A skin lesion imaged with a dermatoscope.
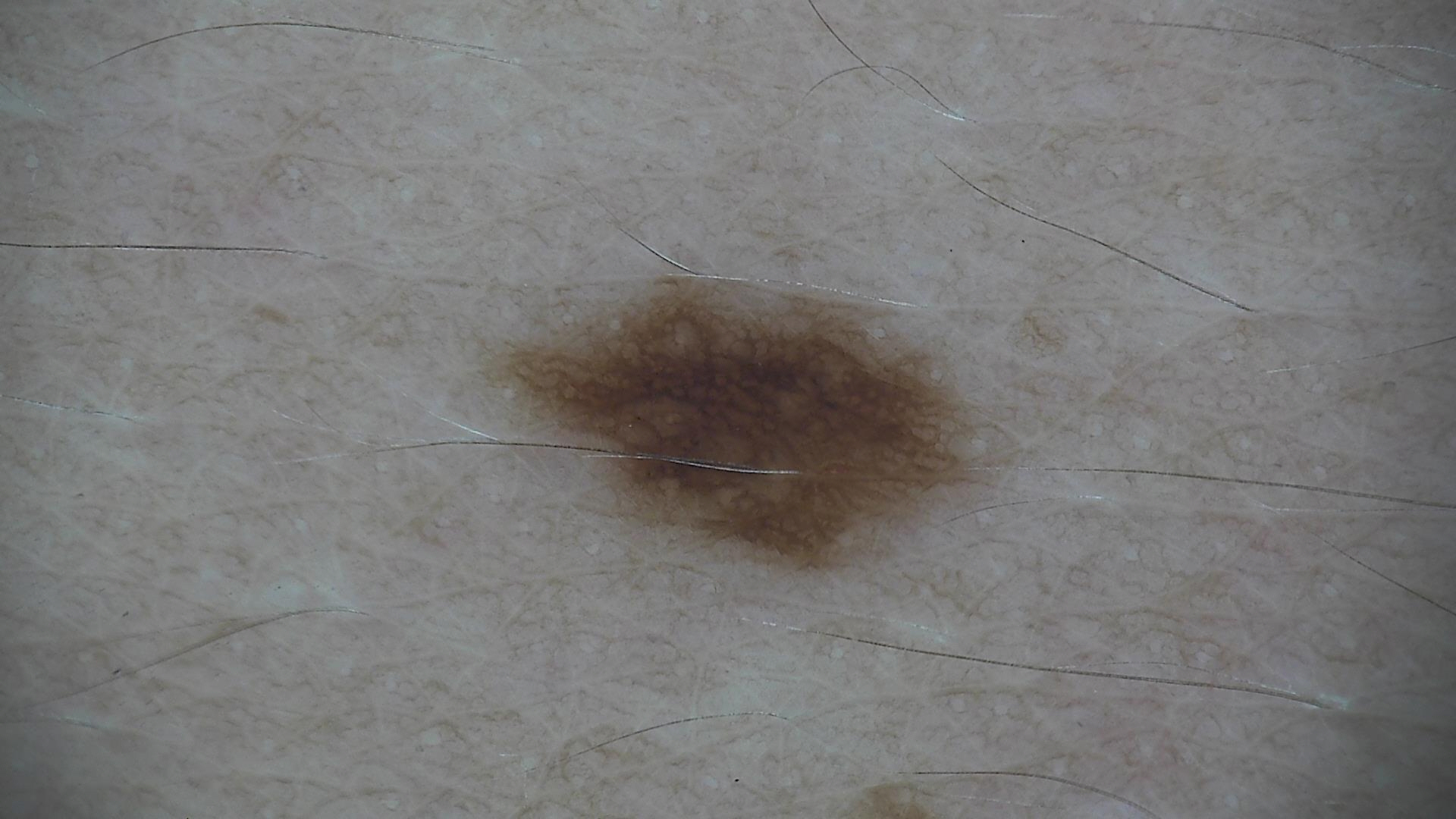The diagnostic label was a dysplastic junctional nevus.